A subject in their 30s; a clinical photo of a skin lesion taken with a smartphone: 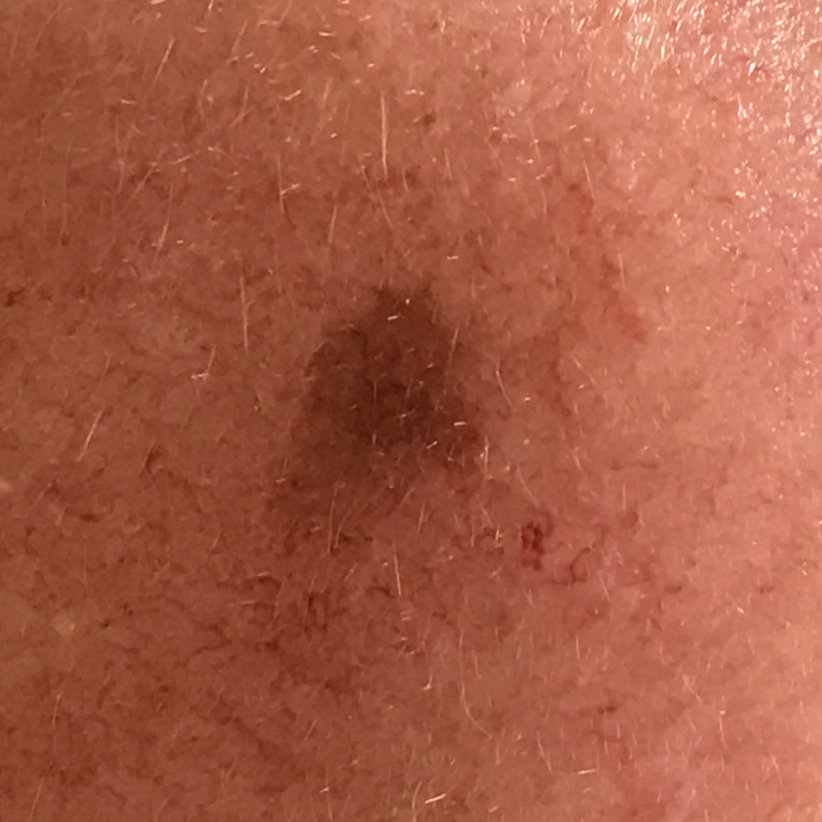anatomic site: the face
symptoms: growth
diagnosis: nevus (clinical consensus)